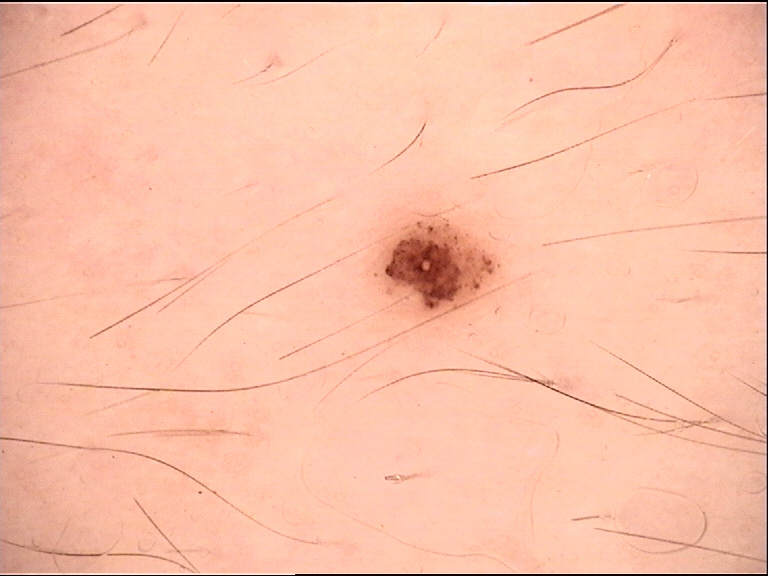| key | value |
|---|---|
| lesion type | banal |
| diagnostic label | compound nevus (expert consensus) |